Skin tone: Fitzpatrick skin type IV; an image taken at a distance; the contributor is 18–29, female — 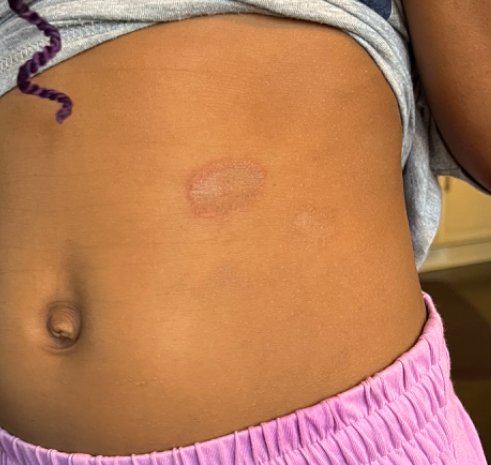Notes:
• differential diagnosis: most likely Tinea; possibly Drug Rash; less likely is Porokeratosis